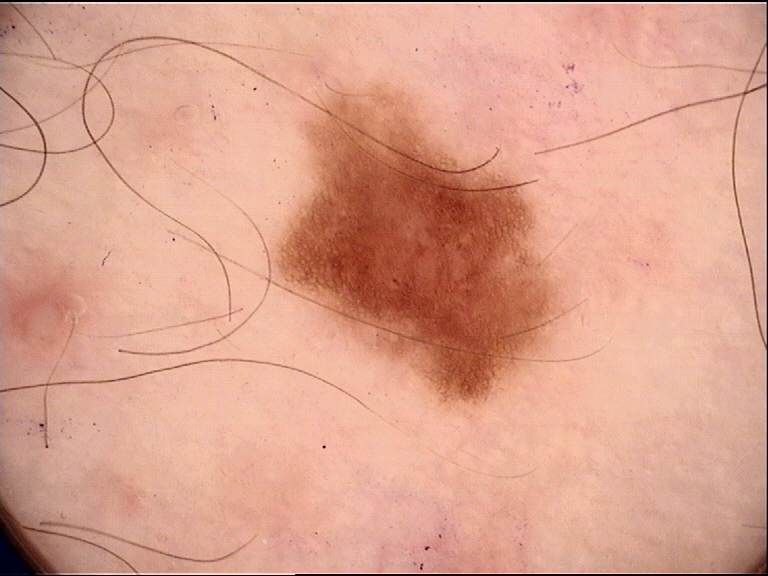Q: What is the imaging modality?
A: dermatoscopy
Q: What is the diagnosis?
A: dysplastic junctional nevus (expert consensus)